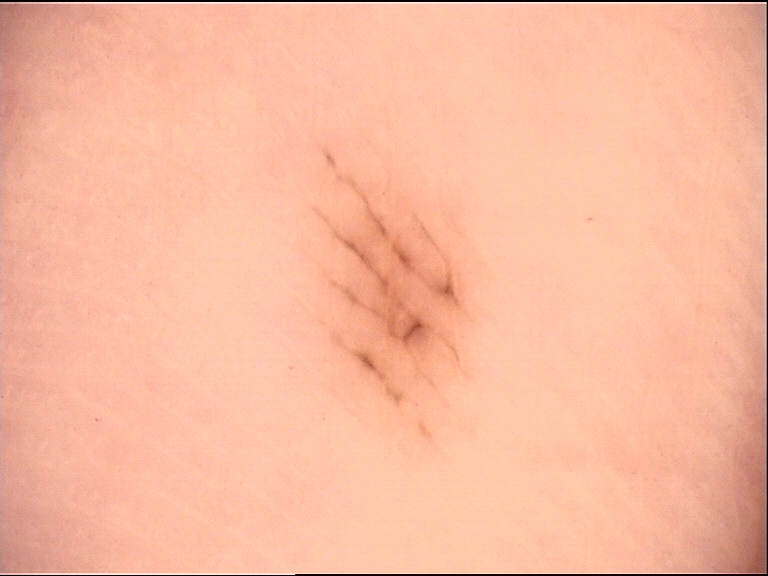Findings: A dermoscopy image of a single skin lesion. The architecture is that of a banal lesion. Impression: Classified as an acral junctional nevus.